An image taken at a distance: 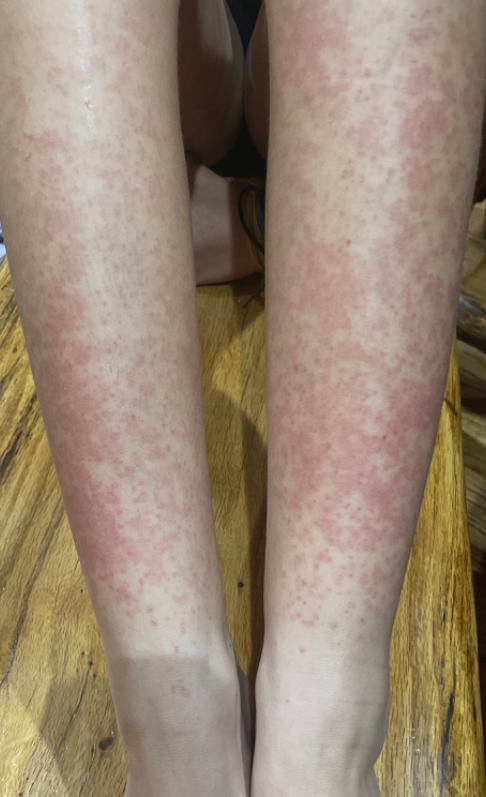On dermatologist assessment of the image: most likely Drug Rash.